The photograph is a close-up of the affected area: 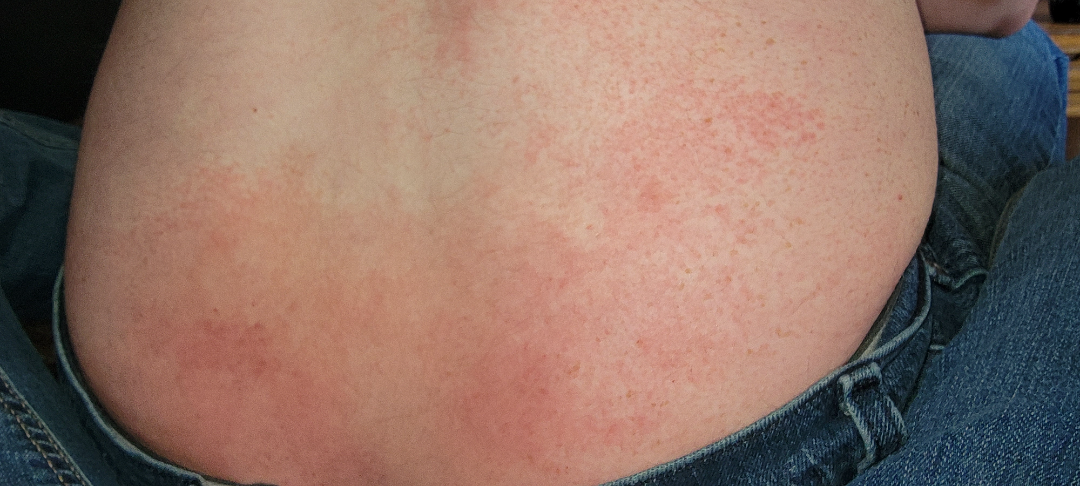assessment = could not be assessed.